The photograph is a close-up of the affected area; located on the head or neck.
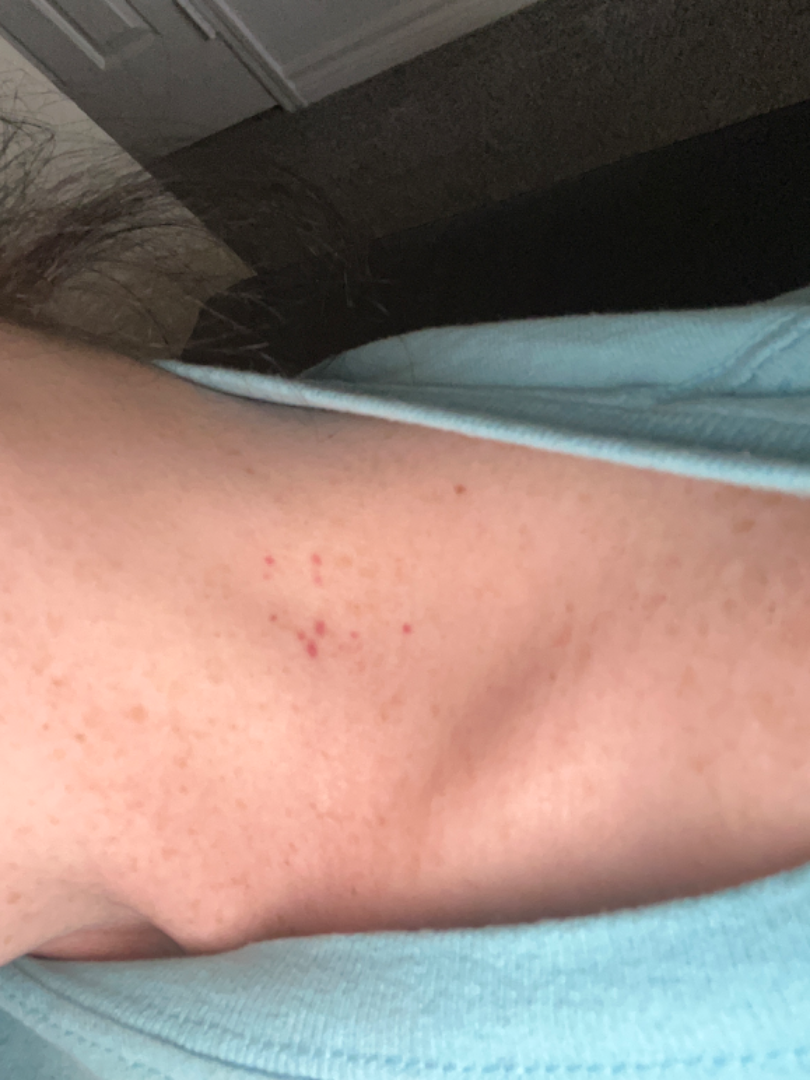assessment: ungradable on photographic review.